A dermatoscopic image of a skin lesion: 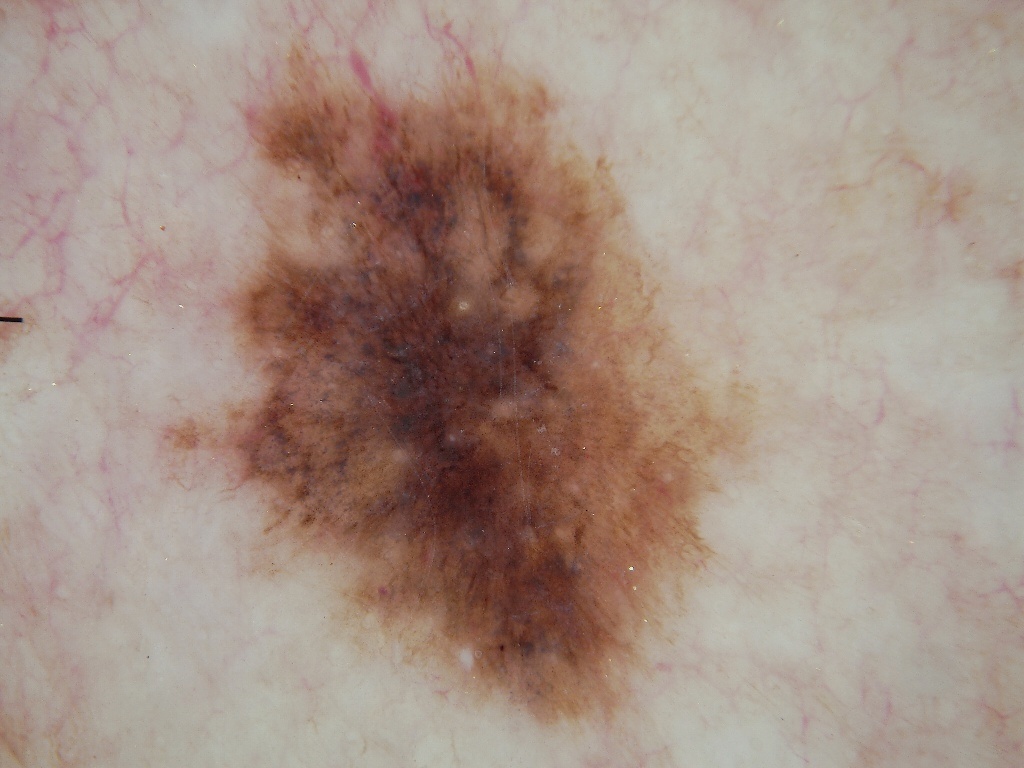lesion bbox — left=157, top=30, right=735, bottom=725
lesion size — ~30% of the field
impression — a malignant skin lesion